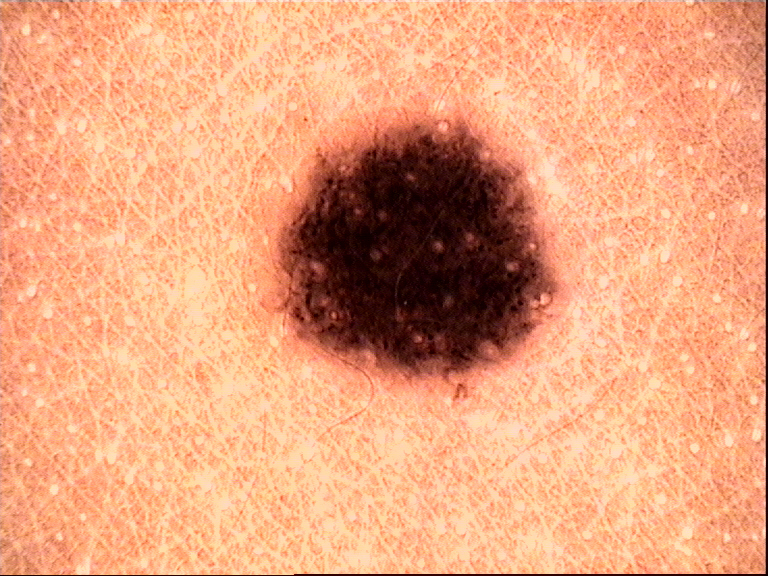A dermoscopic close-up of a skin lesion.
Classified as a benign lesion — a dysplastic compound nevus.